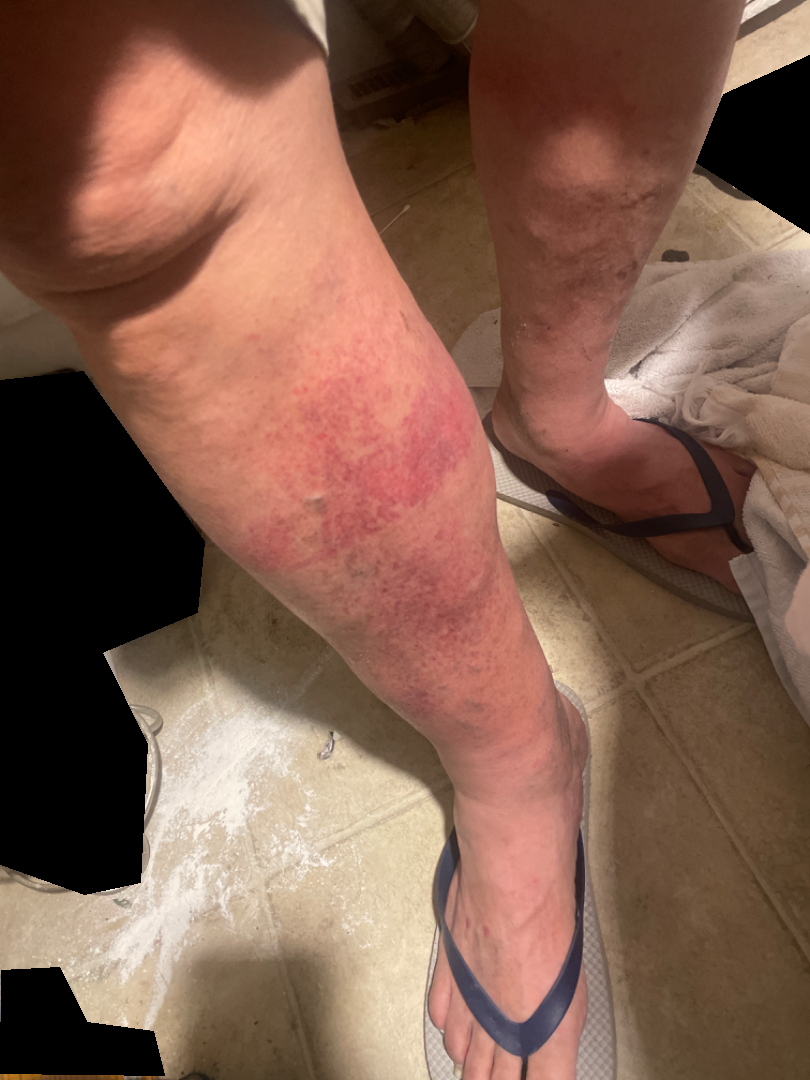Q: What was the assessment?
A: not assessable
Q: How was the photo taken?
A: close-up
Q: Fitzpatrick or Monk tone?
A: self-reported FST VI; human graders estimated Monk Skin Tone 2 or 3 (two reviewer pools)
Q: How long has this been present?
A: one to four weeks
Q: Reported symptoms?
A: none reported
Q: How does the lesion feel?
A: flat
Q: Age and sex?
A: male, age 60–69
Q: How does the patient describe it?
A: a rash
Q: Constitutional symptoms?
A: none reported
Q: Anatomic location?
A: leg